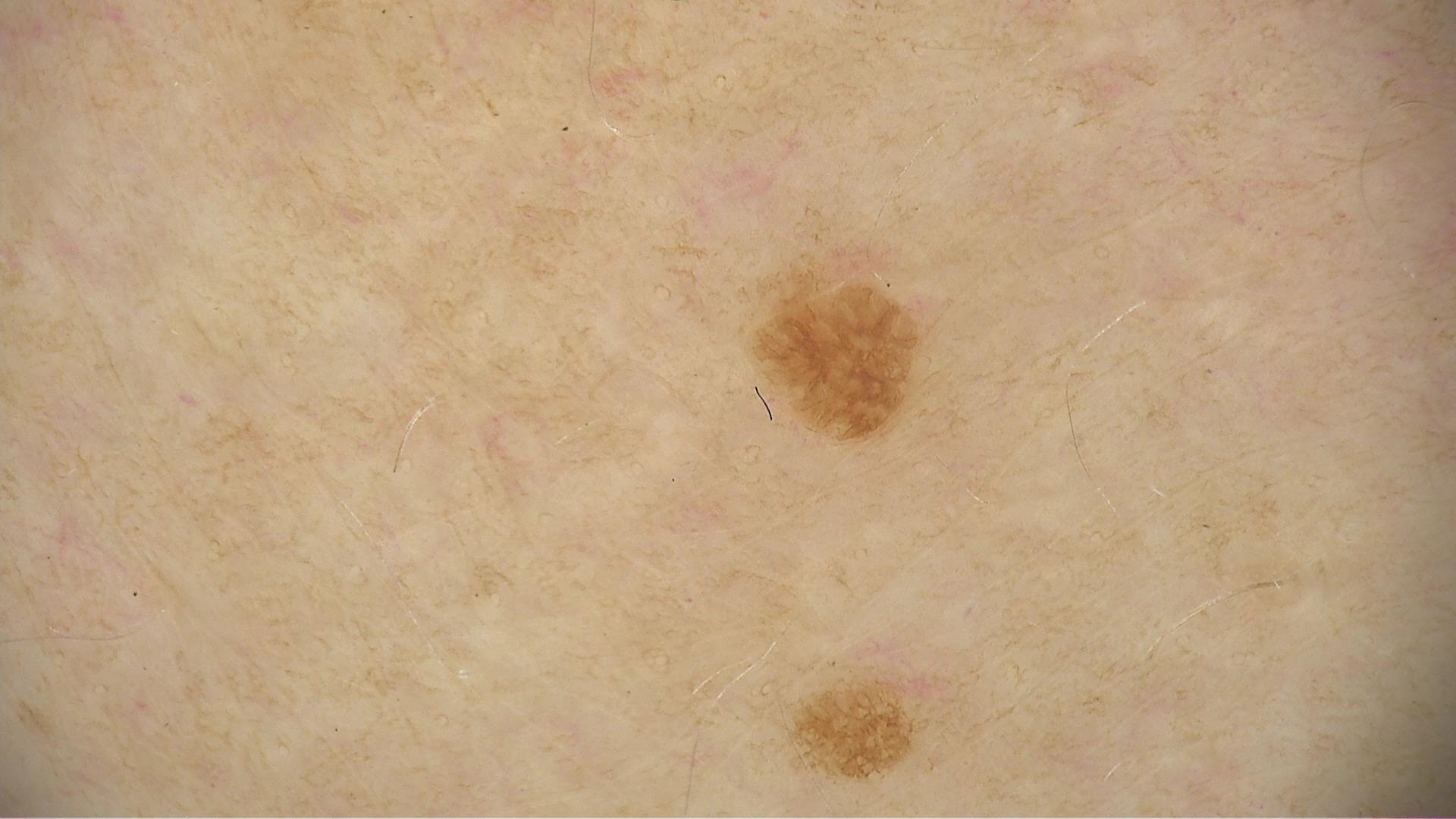Summary: A dermoscopy image of a single skin lesion. Impression: Labeled as a keratinocytic, benign lesion — a seborrheic keratosis.